A close-up photograph. Female contributor, age 40–49. The affected area is the front of the torso, back of the torso and arm.
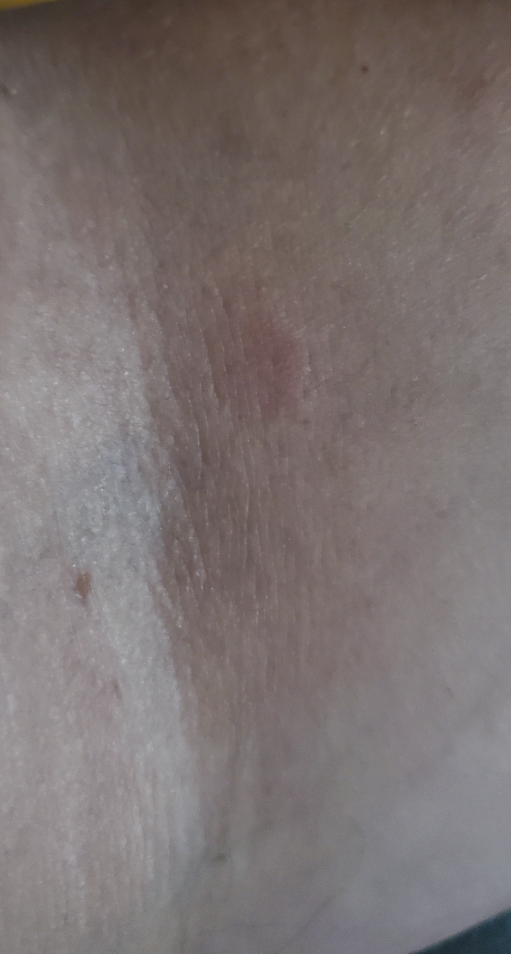Assessment: The reviewing dermatologist's impression was: the leading consideration is Eczema; also raised was Acute and chronic dermatitis.